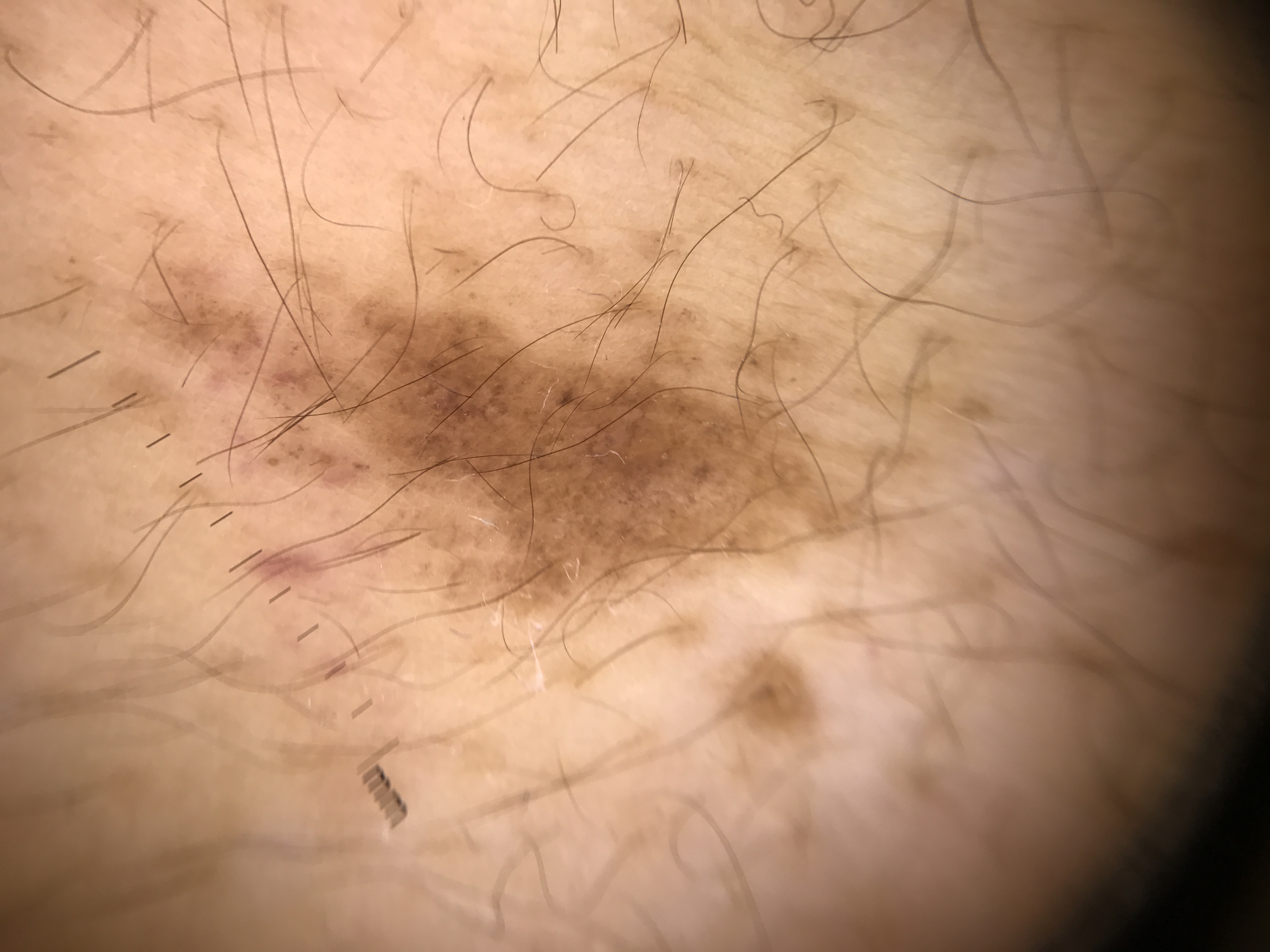A dermoscopic close-up of a skin lesion.
The diagnosis was a dysplastic junctional nevus.